Present for about one day. The photo was captured at an angle. The lesion is associated with itching. The patient considered this a rash. Located on the arm and back of the hand. Texture is reported as raised or bumpy. Fitzpatrick phototype V.
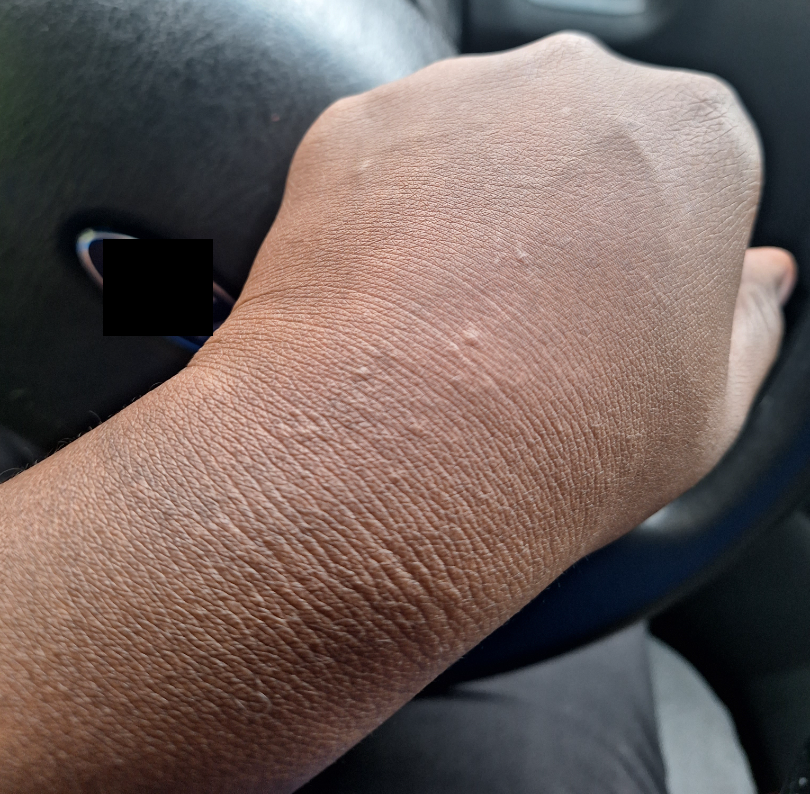Findings:
– diagnostic considerations: consistent with Chronic dermatitis, NOS